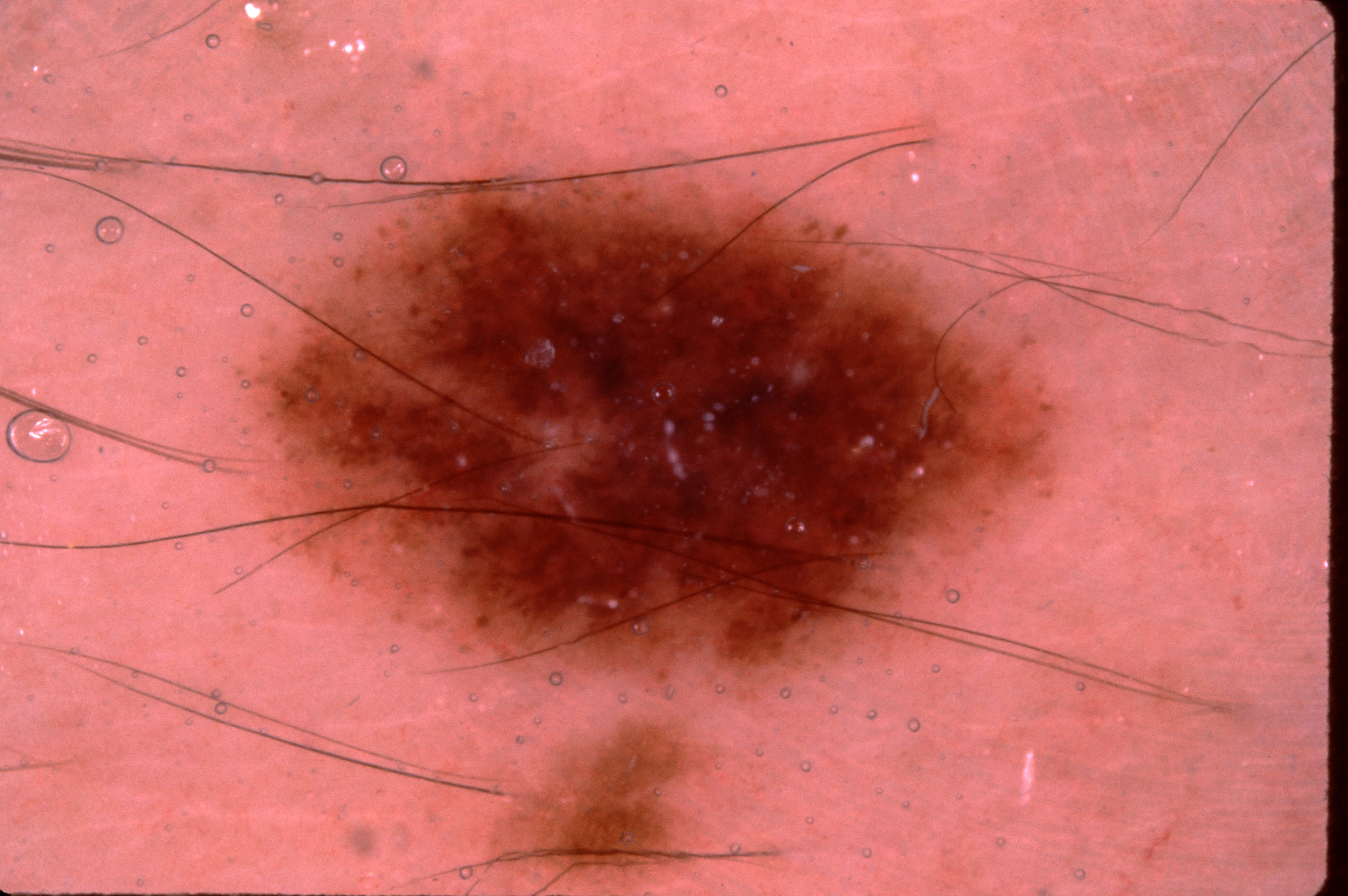Case summary:
- imaging · dermoscopy
- subject · male, aged approximately 40
- size · ~24% of the field
- lesion location · <bbox>263, 175, 1053, 679</bbox>
- dermoscopic features not present · milia-like cysts, pigment network, negative network, and streaks
- assessment · a melanocytic nevus